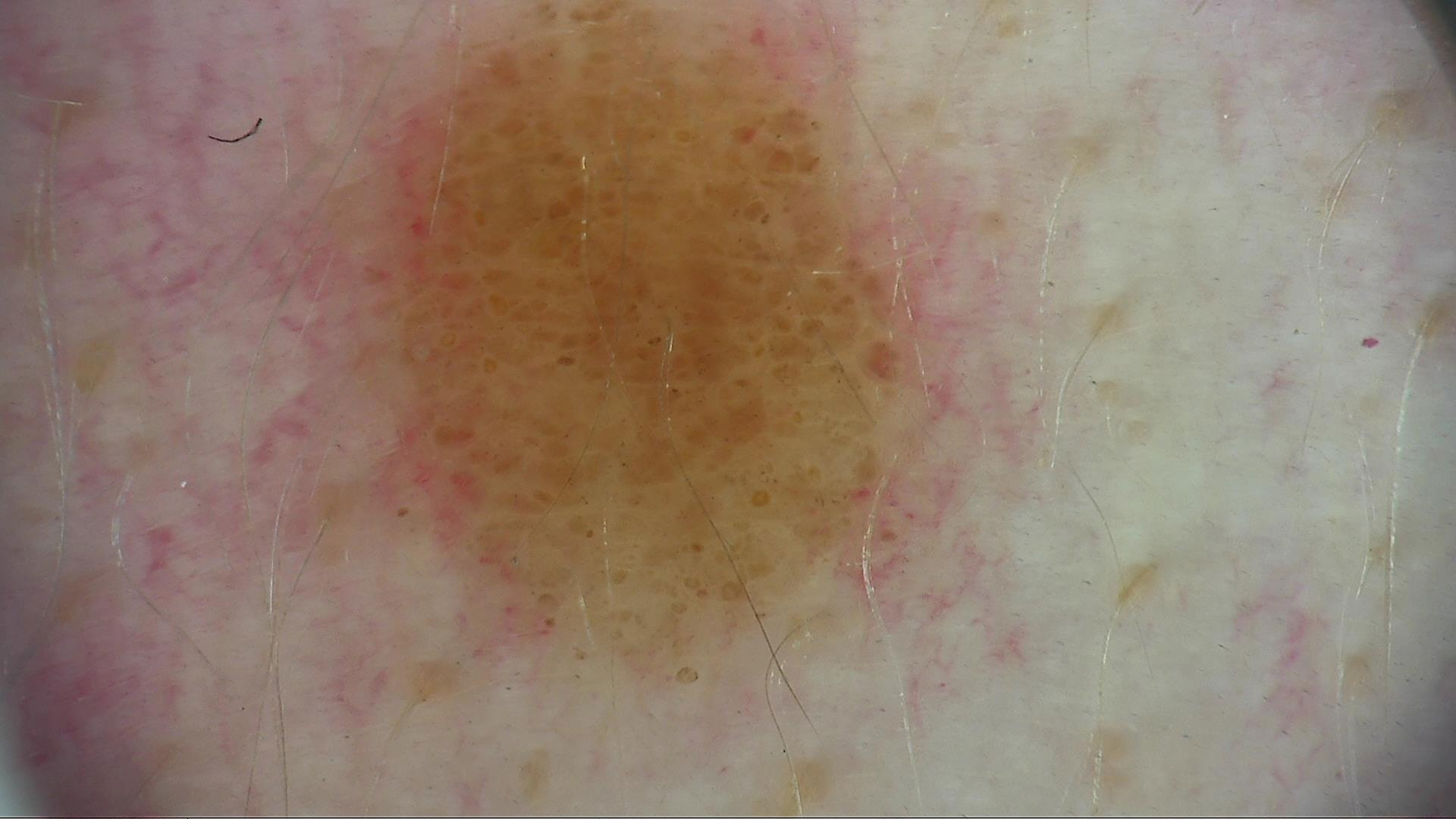| feature | finding |
|---|---|
| image type | dermoscopy |
| diagnostic label | compound nevus (expert consensus) |